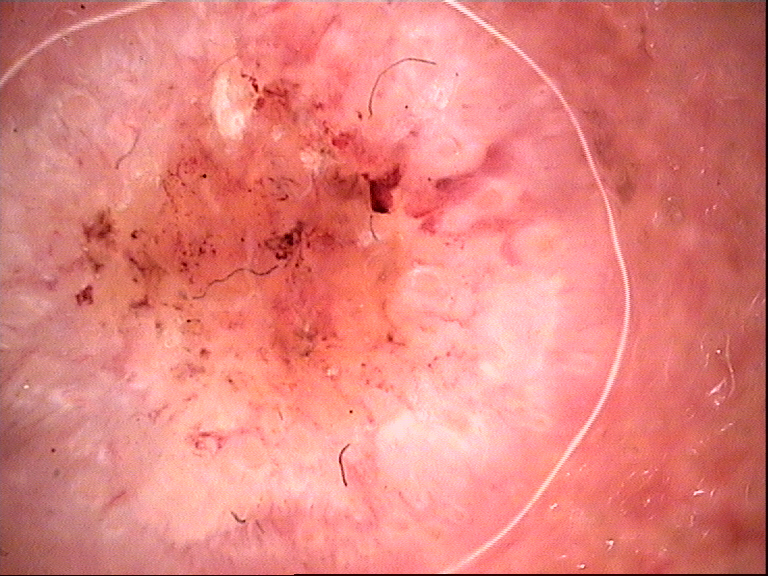Q: How is the lesion classified?
A: keratinocytic
Q: What did the workup show?
A: squamous cell carcinoma (biopsy-proven)